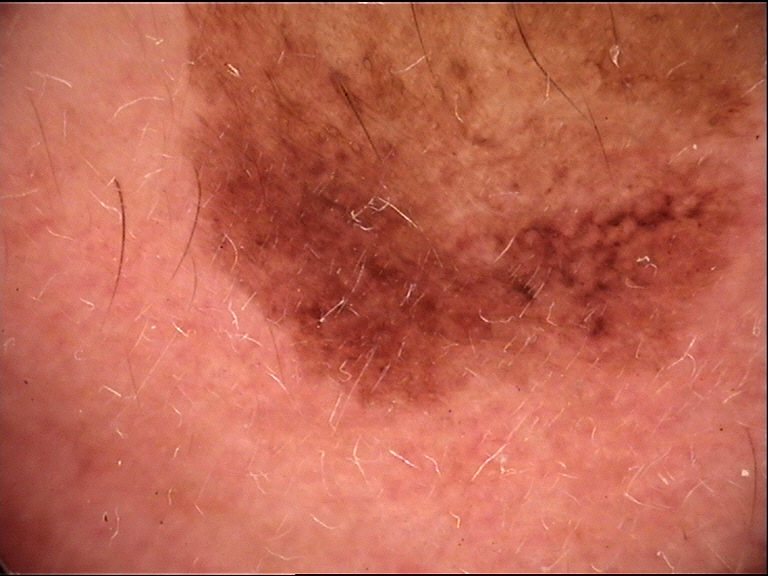Case:
– diagnostic label — lentigo maligna (biopsy-proven)